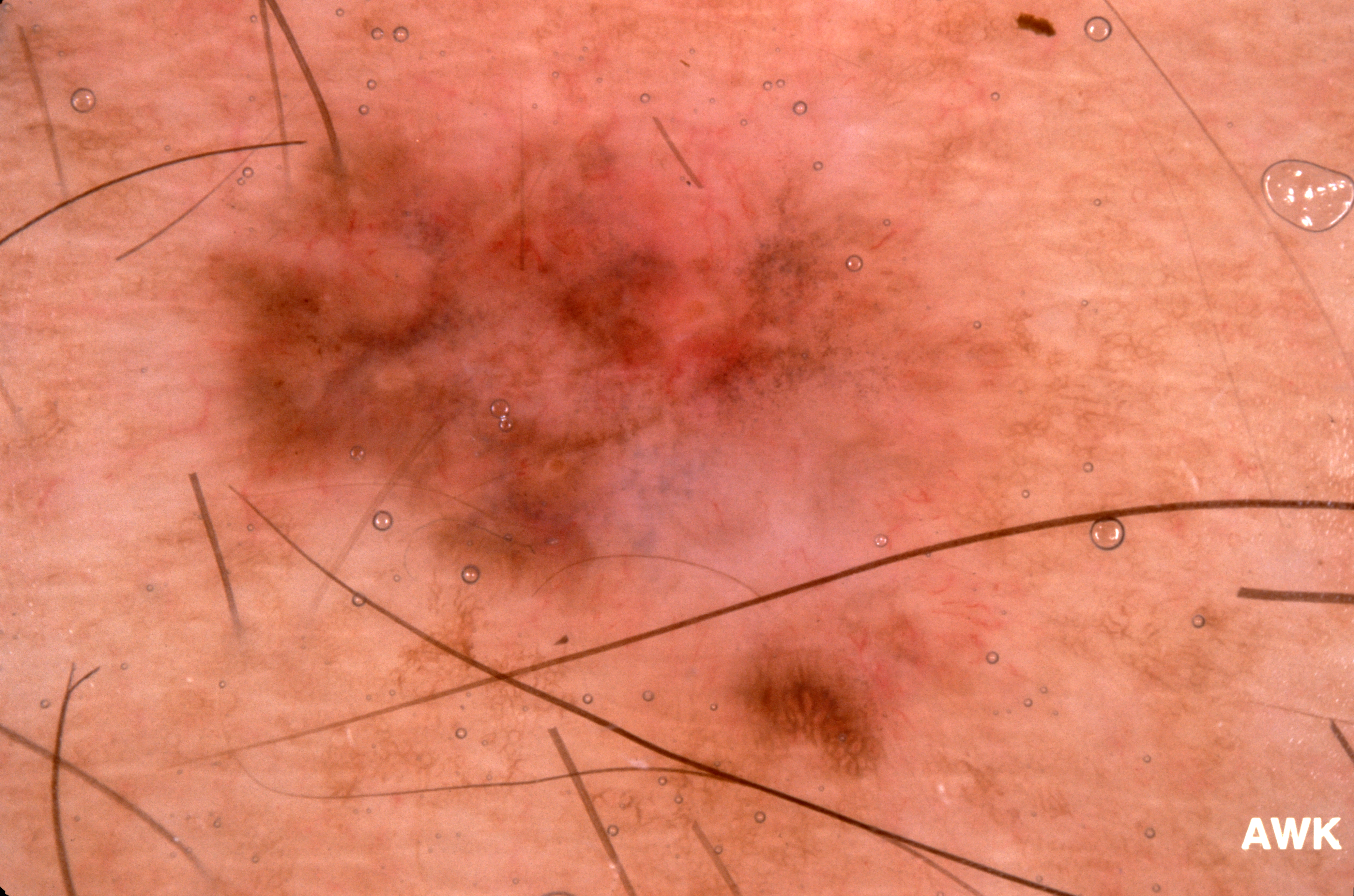<lesion>
<image>
  <modality>dermoscopy</modality>
</image>
<patient>
  <sex>male</sex>
  <age_approx>60</age_approx>
</patient>
<dermoscopic_features>
  <present>pigment network</present>
  <absent>streaks, milia-like cysts, negative network</absent>
</dermoscopic_features>
<lesion_extent>large</lesion_extent>
<lesion_location>
  <bbox_xyxy>161, 51, 1108, 807</bbox_xyxy>
</lesion_location>
<diagnosis>
  <name>melanoma</name>
  <malignancy>malignant</malignancy>
  <lineage>melanocytic</lineage>
  <provenance>histopathology</provenance>
</diagnosis>
</lesion>